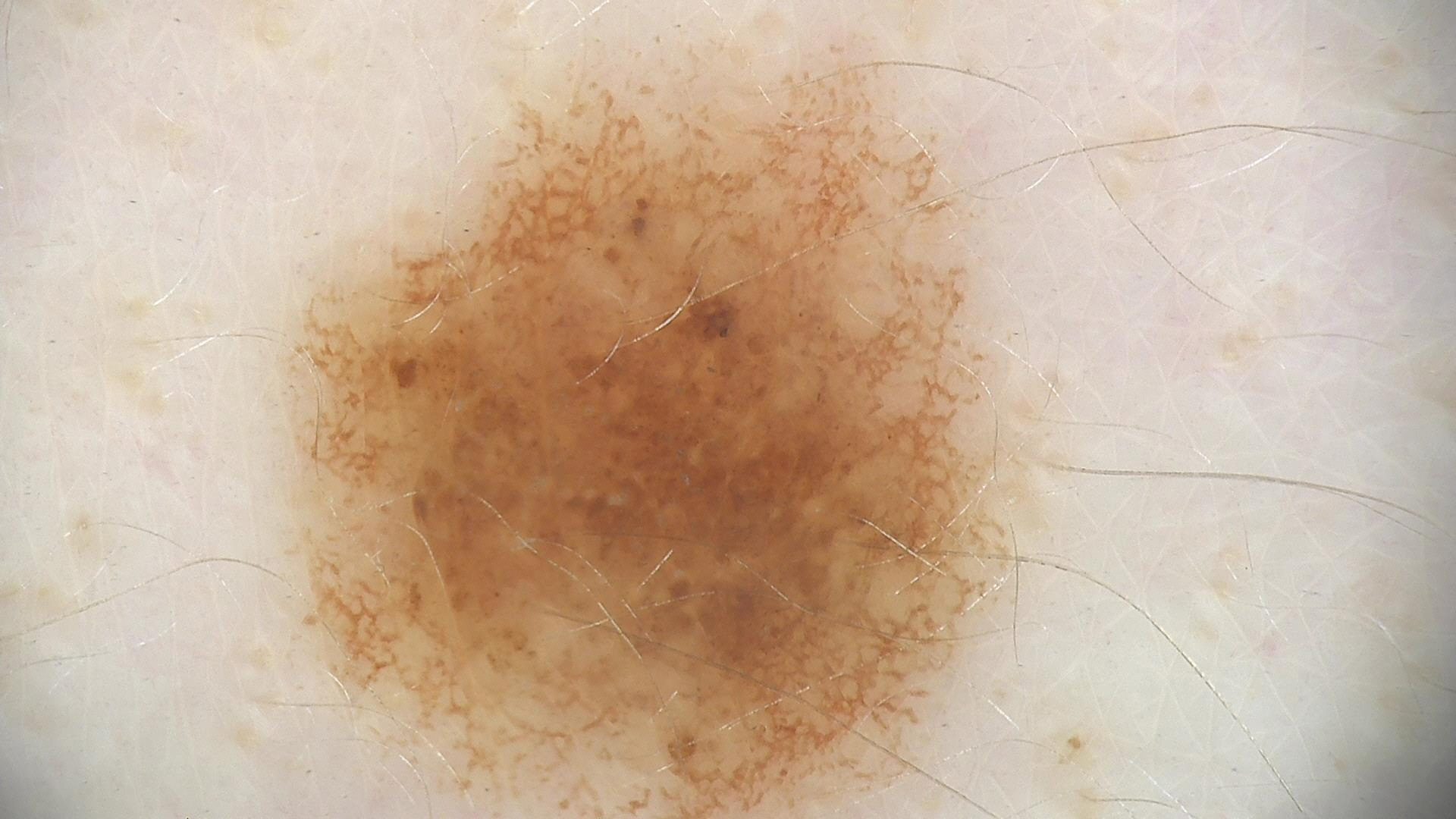class: dysplastic junctional nevus (expert consensus).